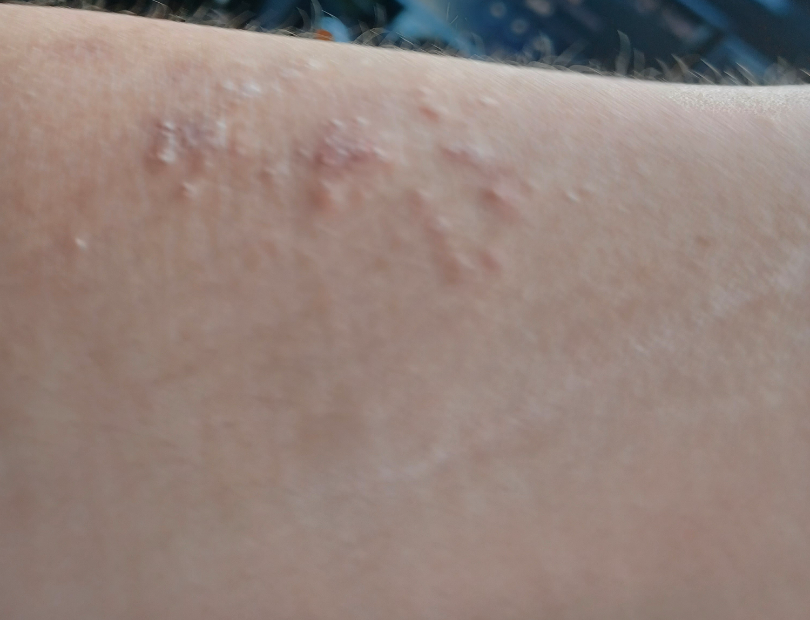History:
The lesion is described as raised or bumpy and rough or flaky. The contributor notes the condition has been present for one to four weeks. The lesion is associated with bothersome appearance. The arm is involved. An image taken at an angle. Associated systemic symptoms include fatigue.
Impression:
On remote dermatologist review, Eczema and Allergic Contact Dermatitis were considered with similar weight; an alternative is Chronic dermatitis, NOS; less likely is Herpes Zoster.